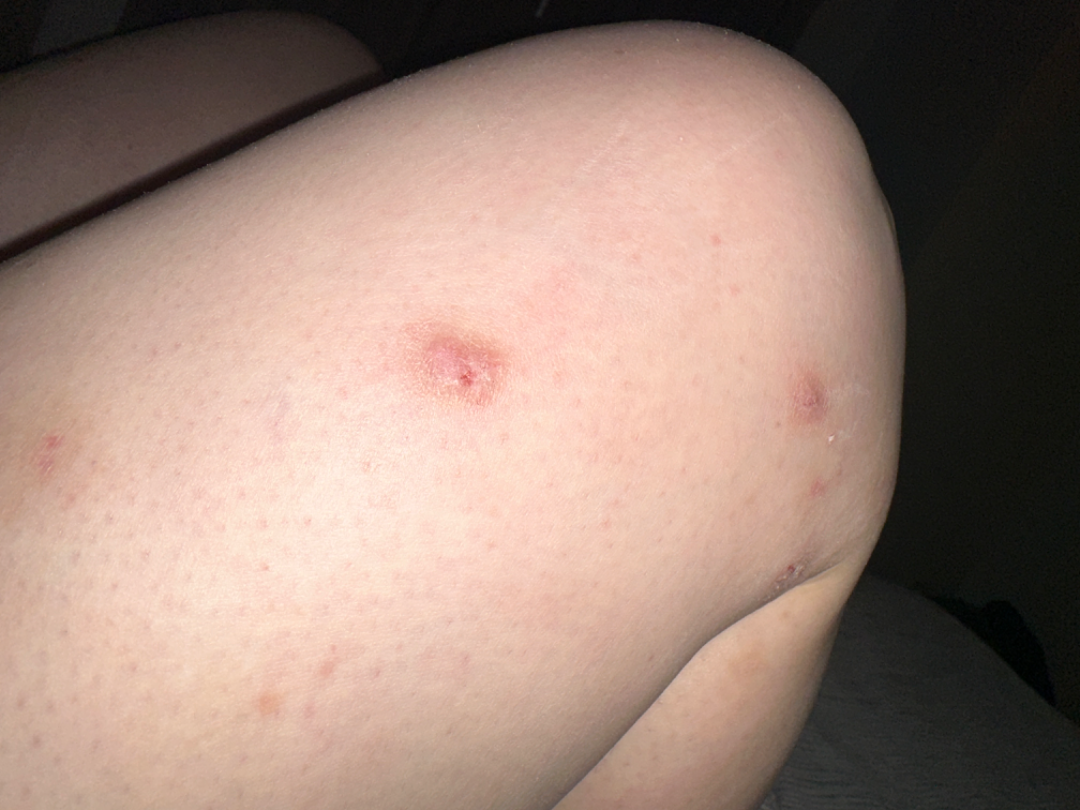assessment: not assessable
image framing: at an angle
patient-reported symptoms: itching
patient: female, age 30–39
texture: raised or bumpy and rough or flaky
body site: leg
present for: since childhood